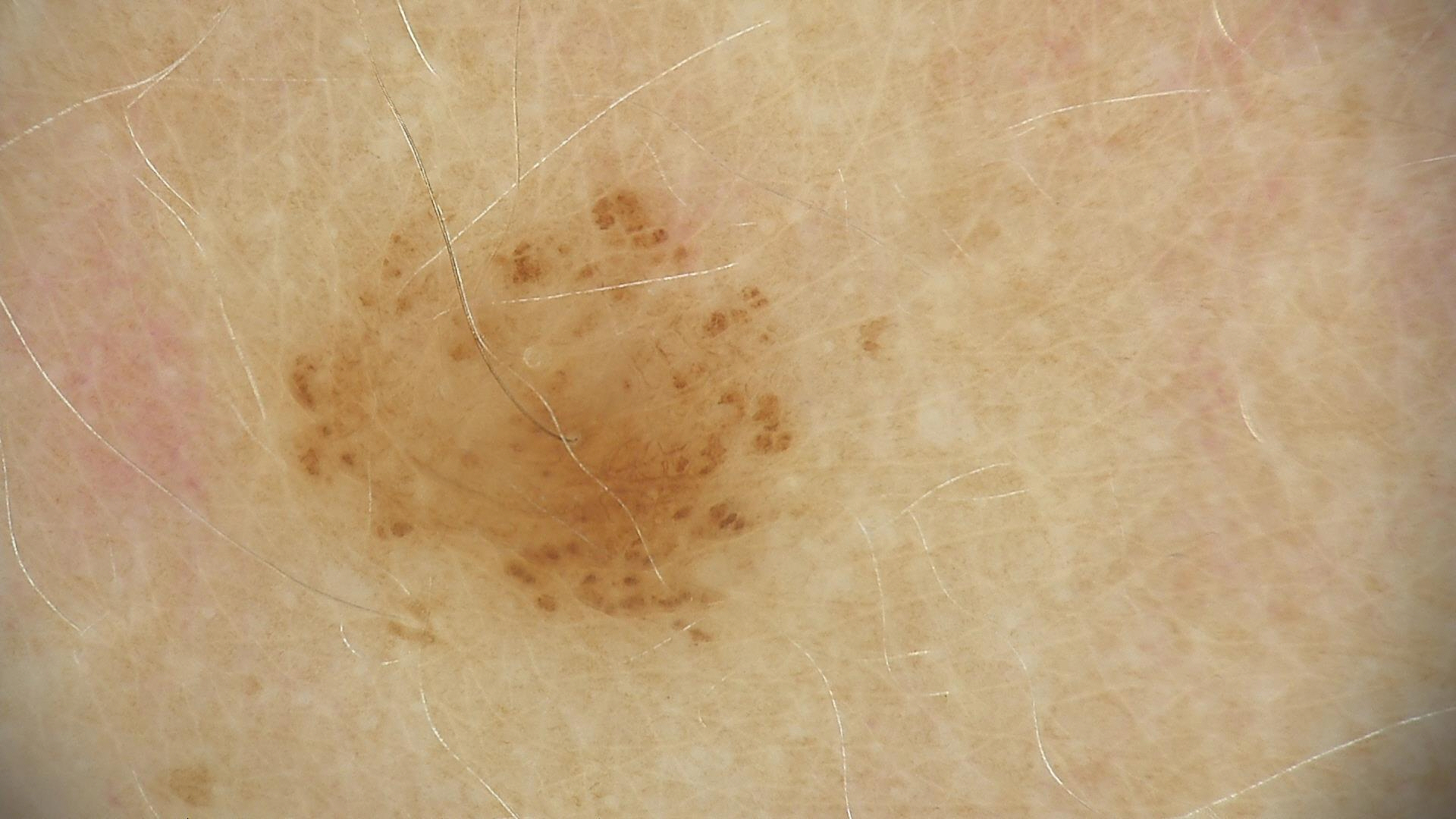Labeled as a dysplastic junctional nevus.